A skin lesion imaged with a dermatoscope. On a questionnaire the patient reported a personal history of cancer and a personal history of skin cancer. The patient says their skin reddens with sun exposure. Acquired for a research image collection, with no referral diagnosis. A moderate number of moles by the patient's own estimate — 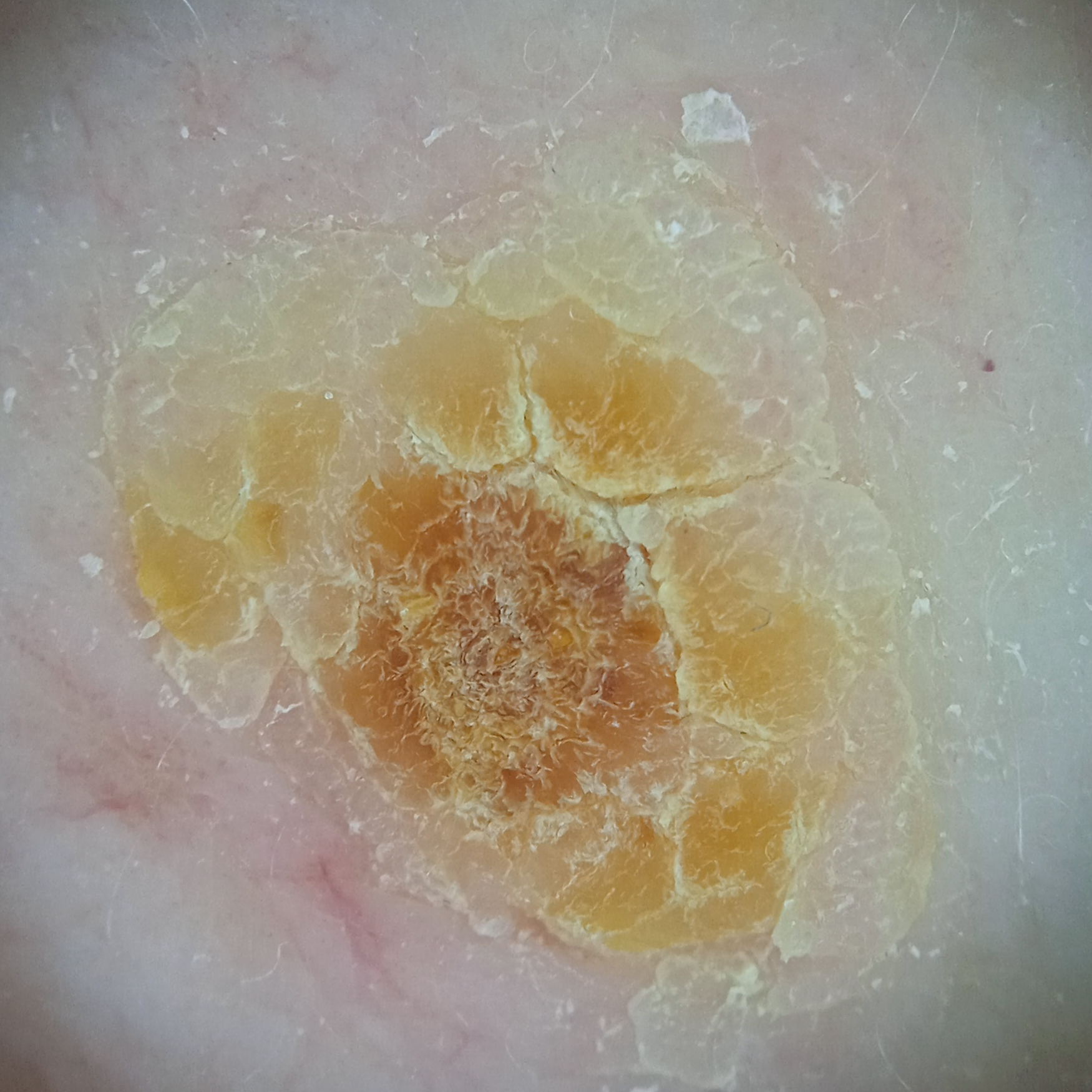Case summary: The lesion measures approximately 11.1 mm. Assessment: The diagnostic impression was an actinic keratosis.